An image taken at an angle · the lesion involves the leg · self-categorized by the patient as a rash · no associated lesion symptoms were reported · reported duration is less than one week · the lesion is described as flat:
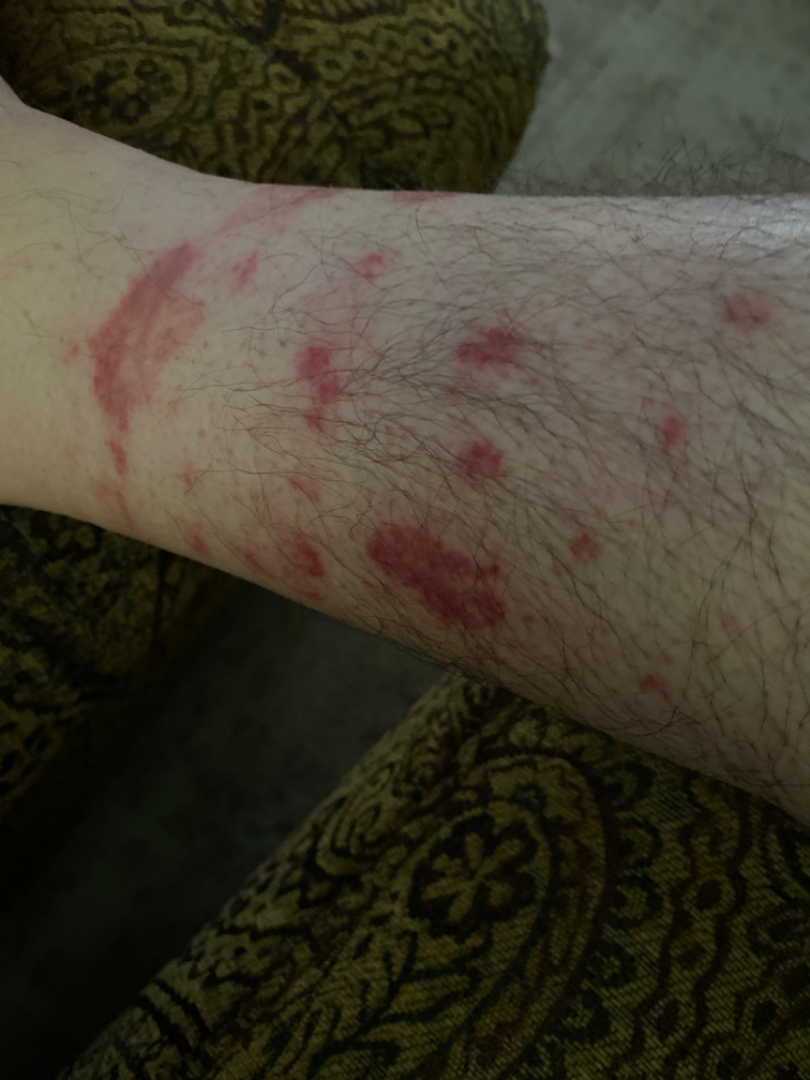On remote dermatologist review, Pigmented purpuric eruption (100%).